A dermoscopic close-up of a skin lesion.
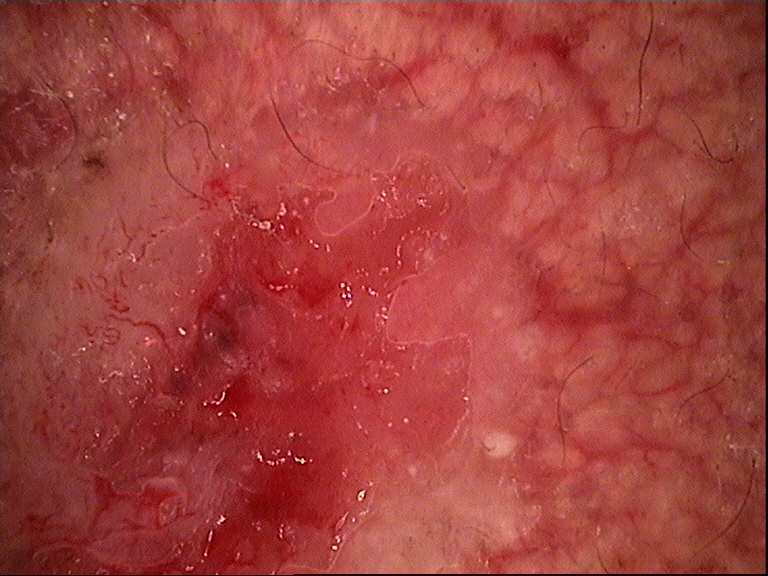Q: What did the workup show?
A: basal cell carcinoma (biopsy-proven)